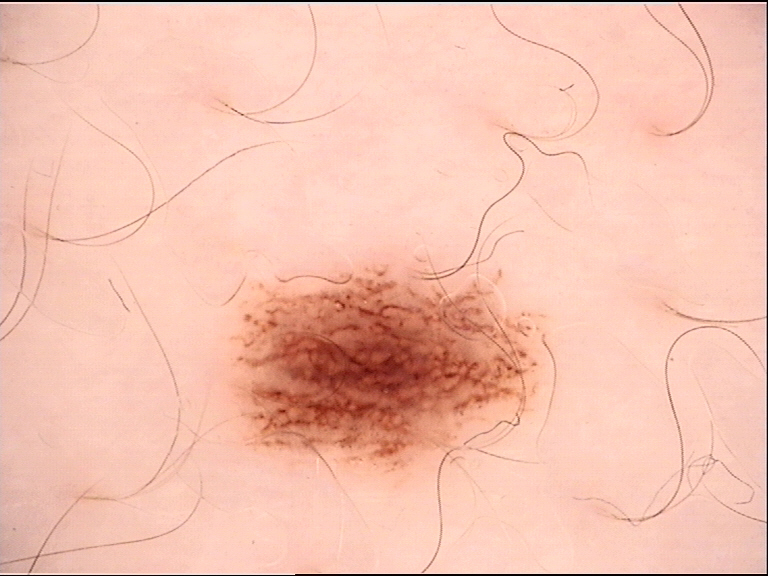Q: What is the diagnosis?
A: dysplastic junctional nevus (expert consensus)